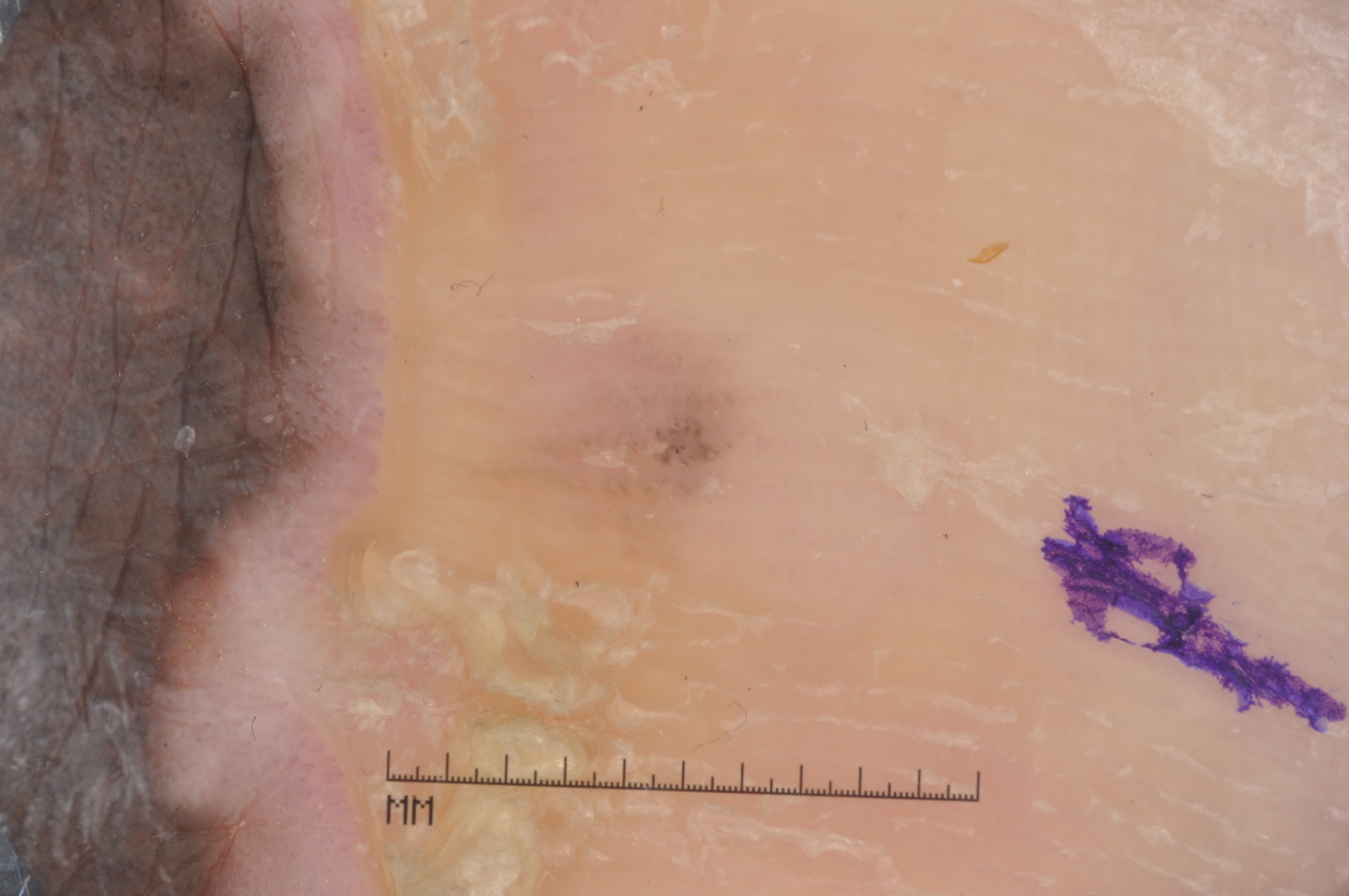{
  "patient": {
    "sex": "female",
    "age_approx": 80
  },
  "image": {
    "modality": "dermoscopy"
  },
  "lesion_location": {
    "bbox_xyxy": [
      1,
      1,
      788,
      895
    ]
  },
  "dermoscopic_features": {
    "present": [],
    "absent": [
      "milia-like cysts",
      "streaks",
      "negative network",
      "pigment network"
    ]
  },
  "lesion_extent": {
    "approx_field_fraction_pct": 53
  },
  "diagnosis": {
    "name": "melanoma",
    "malignancy": "malignant",
    "lineage": "melanocytic",
    "provenance": "histopathology"
  }
}